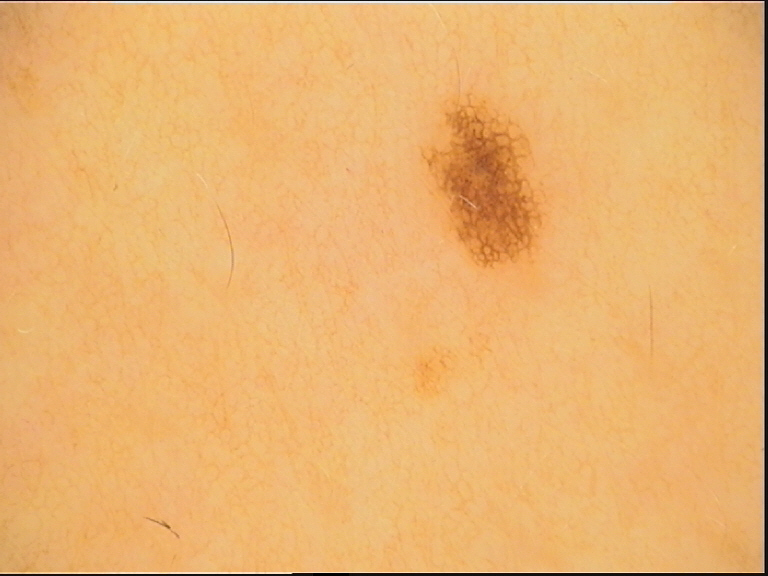label = junctional nevus (expert consensus).